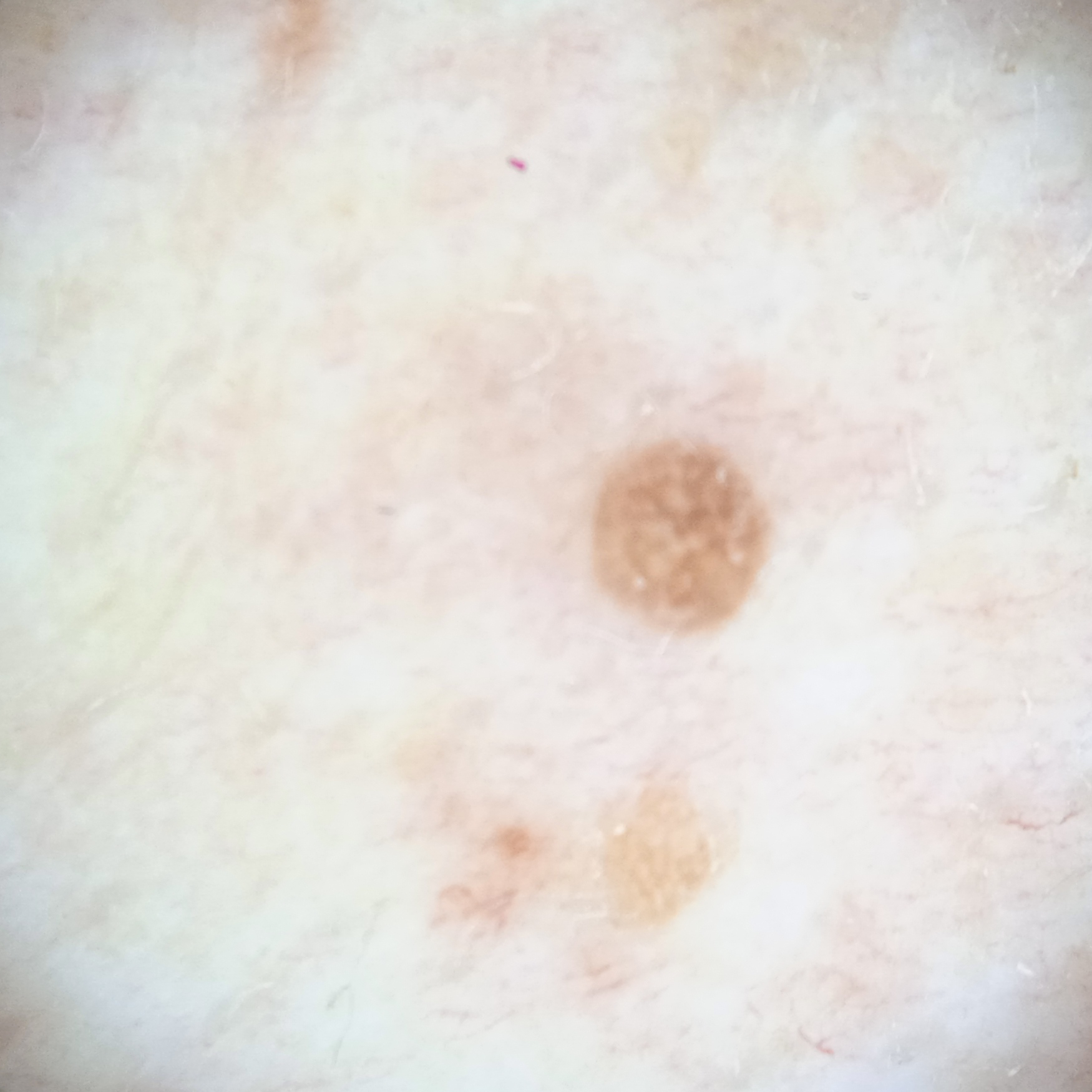imaging: dermoscopy; nevus count: a moderate number of melanocytic nevi; sun reaction: skin reddens with sun exposure; anatomic site: the torso; diameter: 2.2 mm; diagnosis: seborrheic keratosis (dermatologist consensus).